The photograph was taken at a distance: 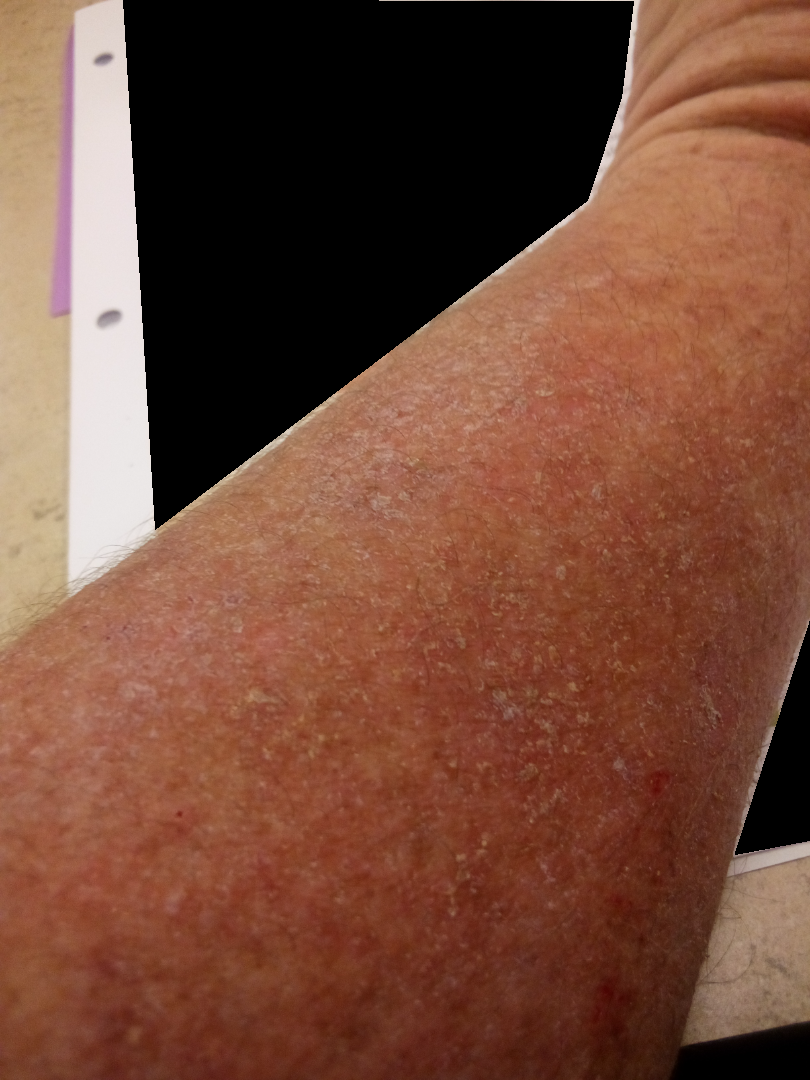assessment: indeterminate from the photograph.